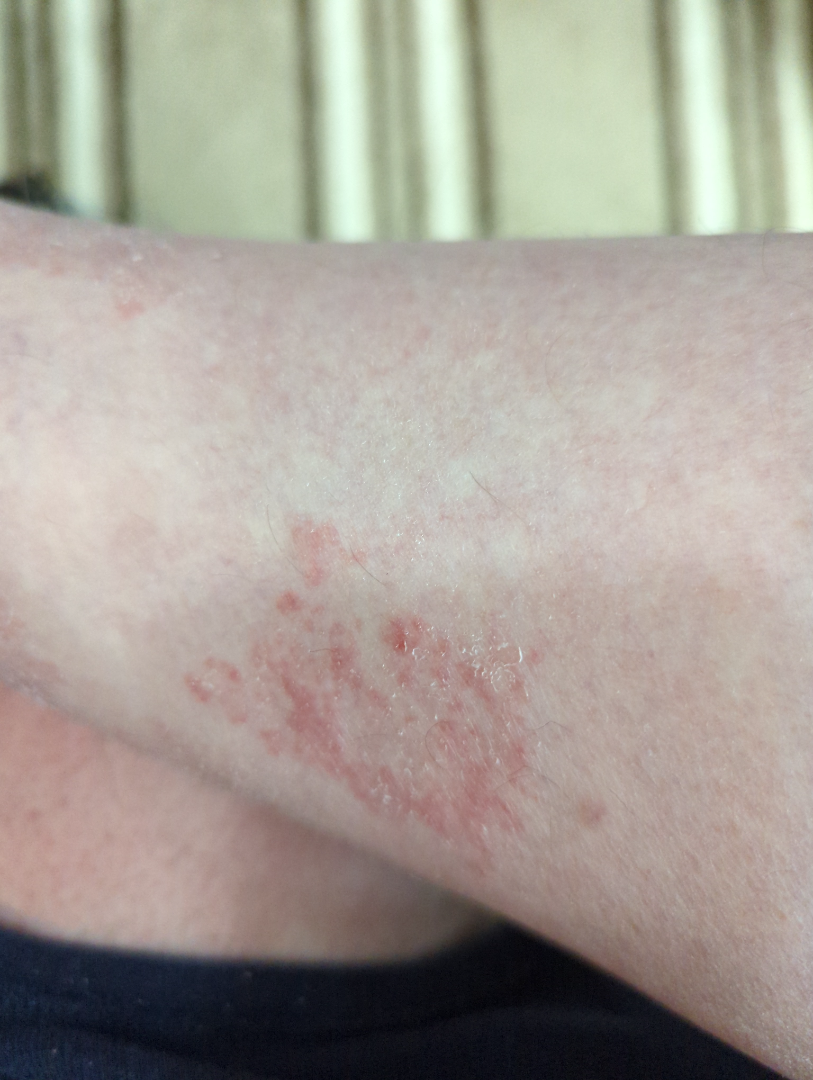diagnostic considerations = favoring Eczema; an alternative is Allergic Contact Dermatitis; possibly Acute dermatitis, NOS; lower on the differential is Tinea; less likely is Stasis Dermatitis